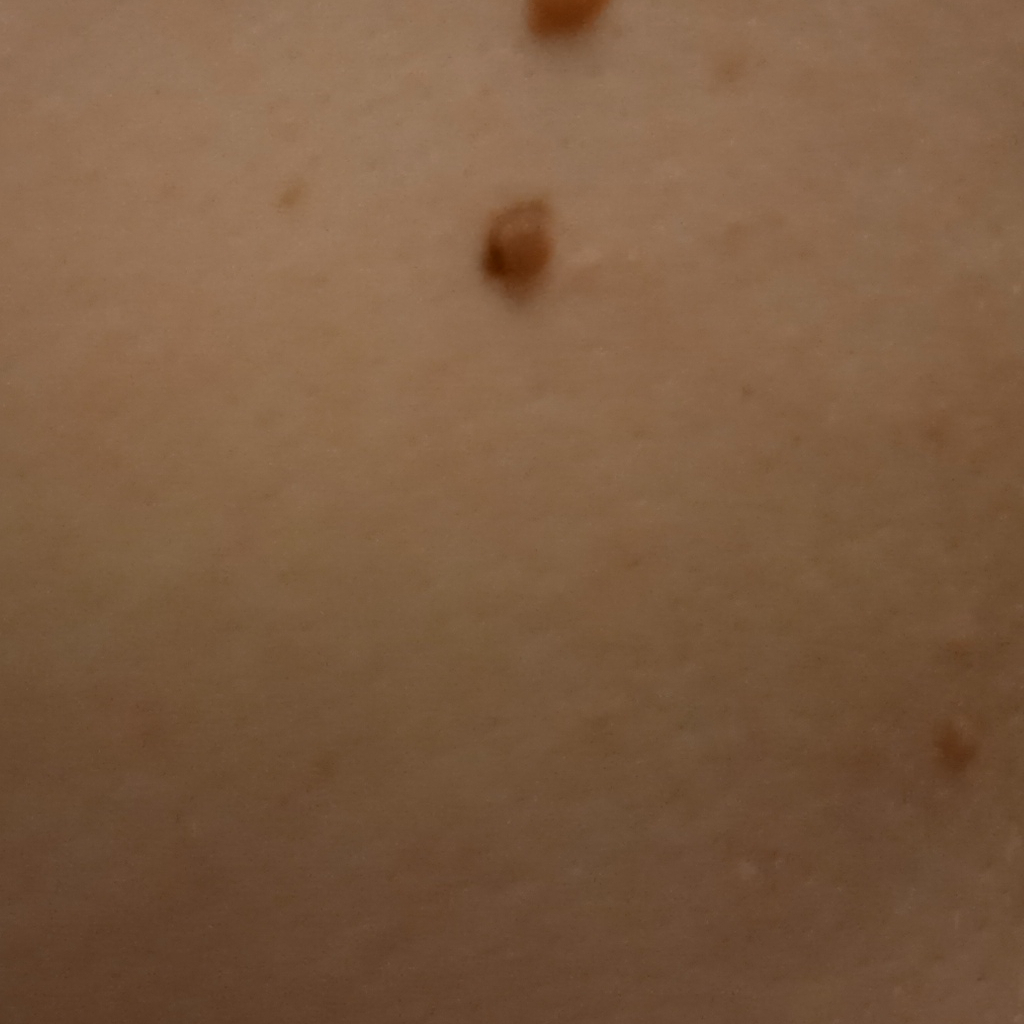Impression:
The lesion was assessed as a melanocytic nevus.